A dermatoscopic image of a skin lesion:
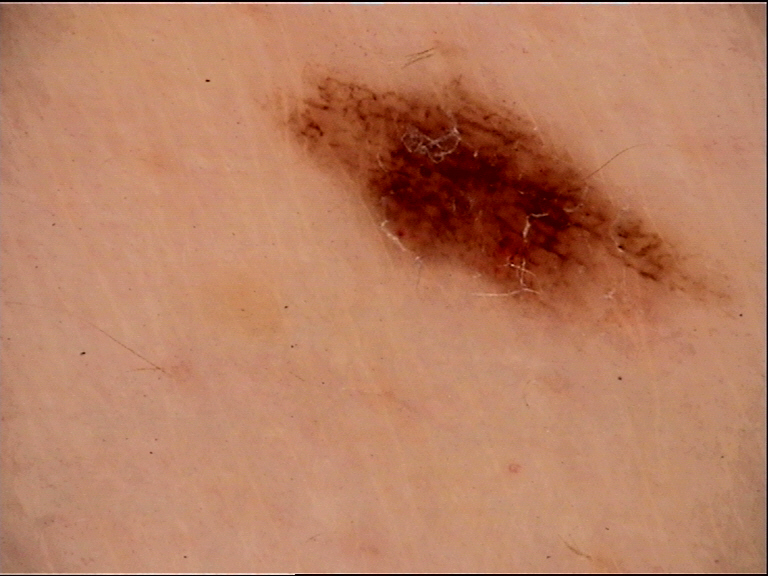The diagnosis was a benign lesion — a dysplastic junctional nevus.